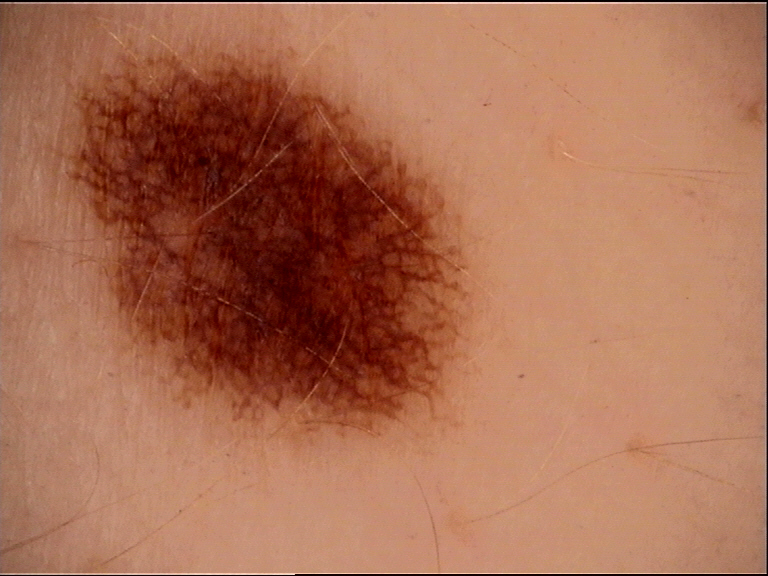<case>
<diagnosis>
<name>dysplastic junctional nevus</name>
<code>jd</code>
<malignancy>benign</malignancy>
<super_class>melanocytic</super_class>
<confirmation>expert consensus</confirmation>
</diagnosis>
</case>